Present for more than one year. This is a close-up image. The patient considered this skin that appeared healthy to them. The patient is 18–29, female. No relevant systemic symptoms. Texture is reported as flat. The patient notes bothersome appearance, enlargement and darkening.
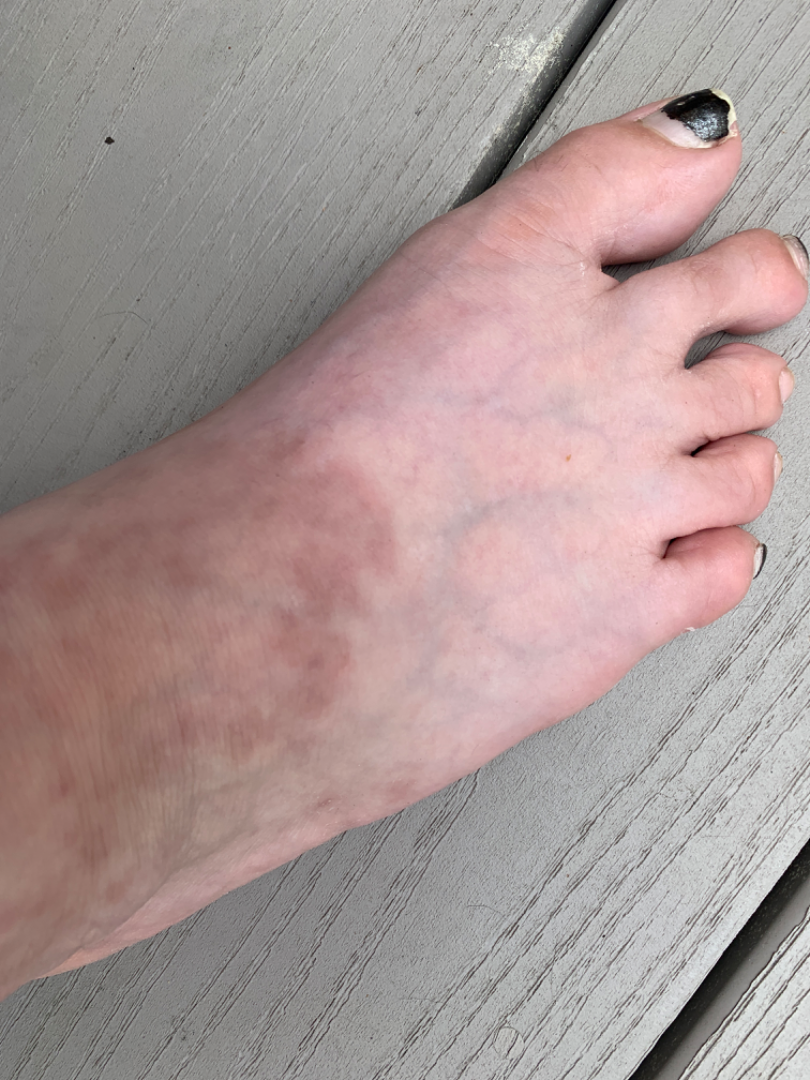On remote dermatologist review, Granuloma annulare (considered); Livedo reticularis (considered); Contact dermatitis (considered); Stasis Dermatitis (remote).